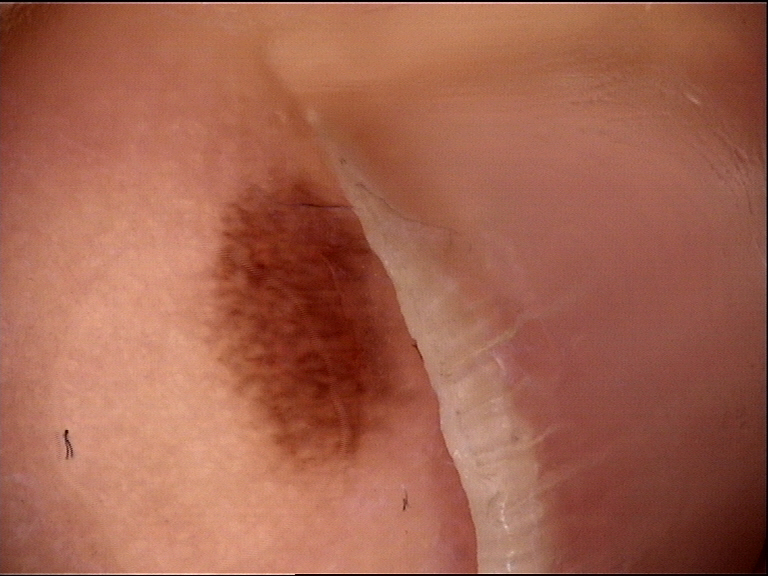Summary: A dermoscopic photograph of a skin lesion. Impression: Labeled as a banal lesion — an acral junctional nevus.